The subject is a male aged 30–39. Located on the leg. A close-up photograph — 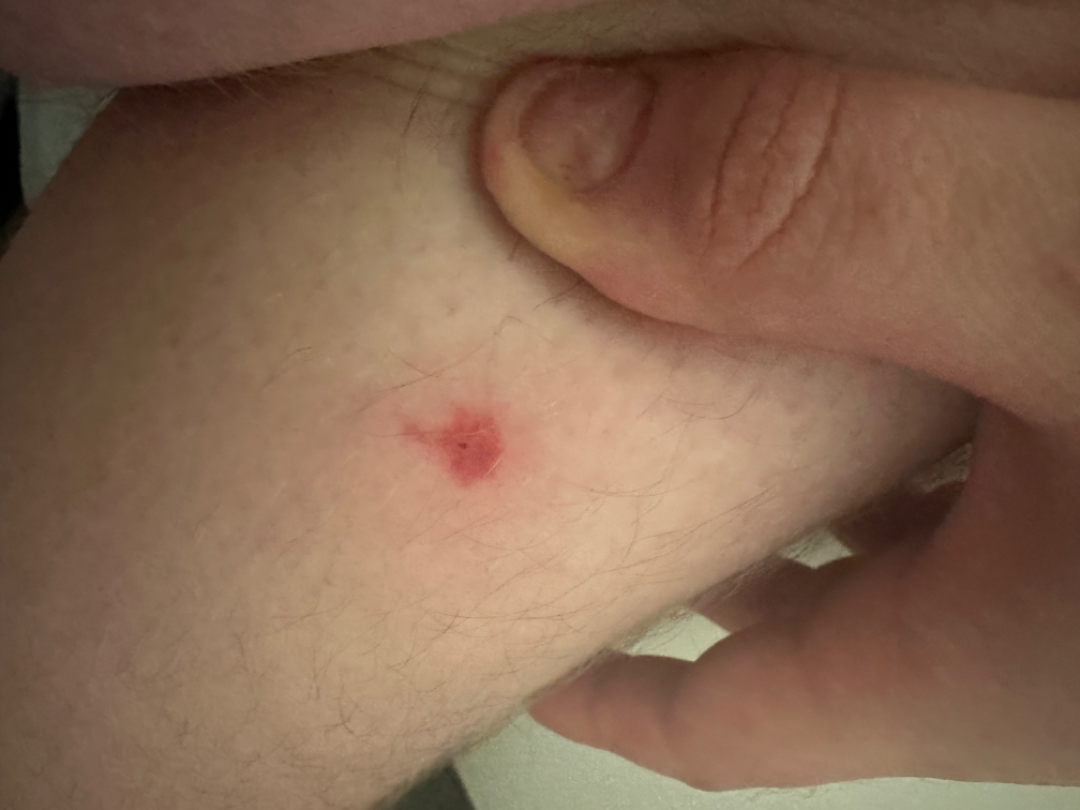History: Texture is reported as flat. The patient indicates the condition has been present for less than one week. Self-categorized by the patient as a rash. The patient indicates bleeding, pain, bothersome appearance and itching. Impression: The reviewing clinician's impression was: Inflicted skin lesions (0.33); Insect Bite (0.33); Localized skin infection (0.33).